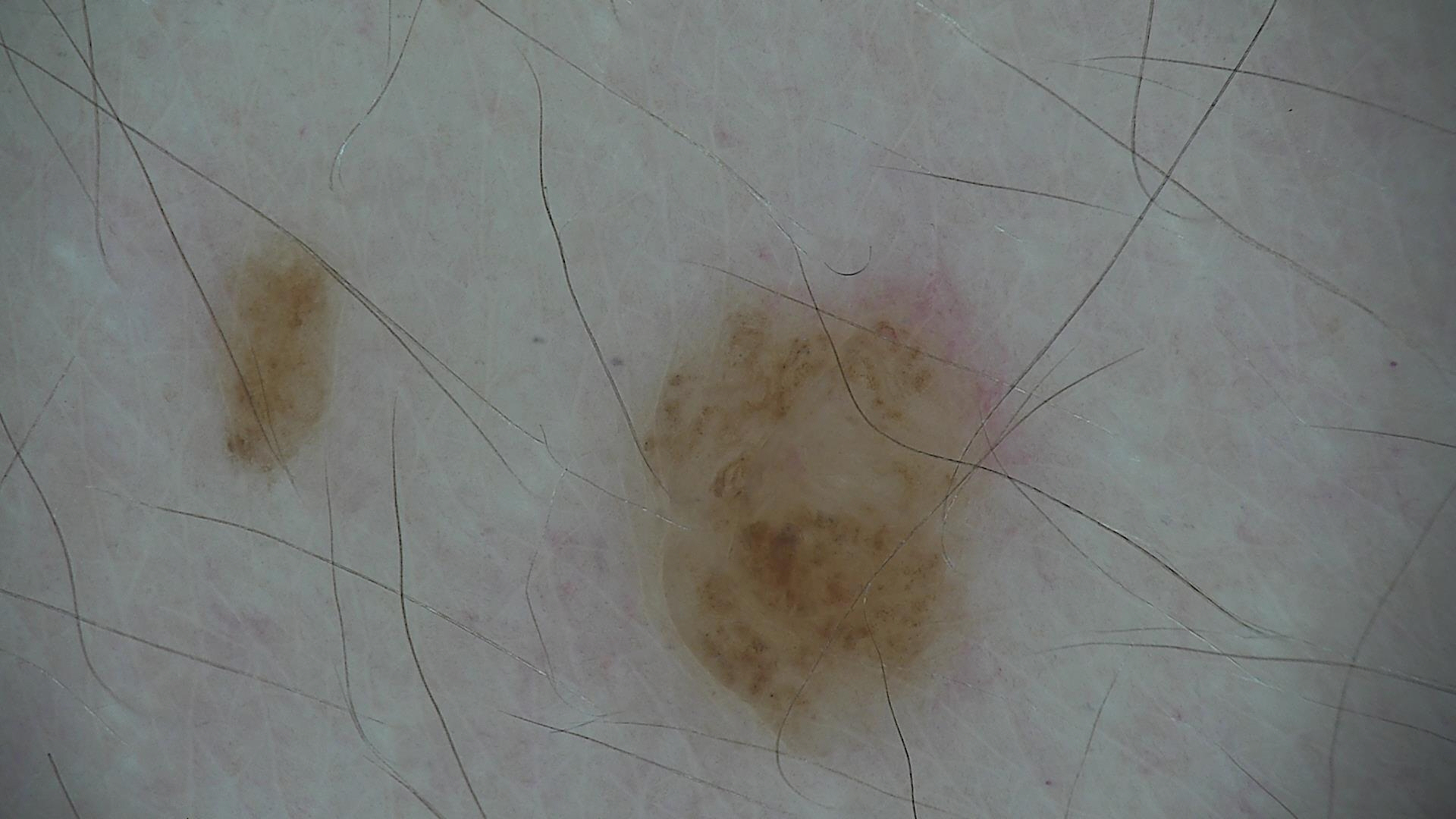– label — compound nevus (expert consensus)